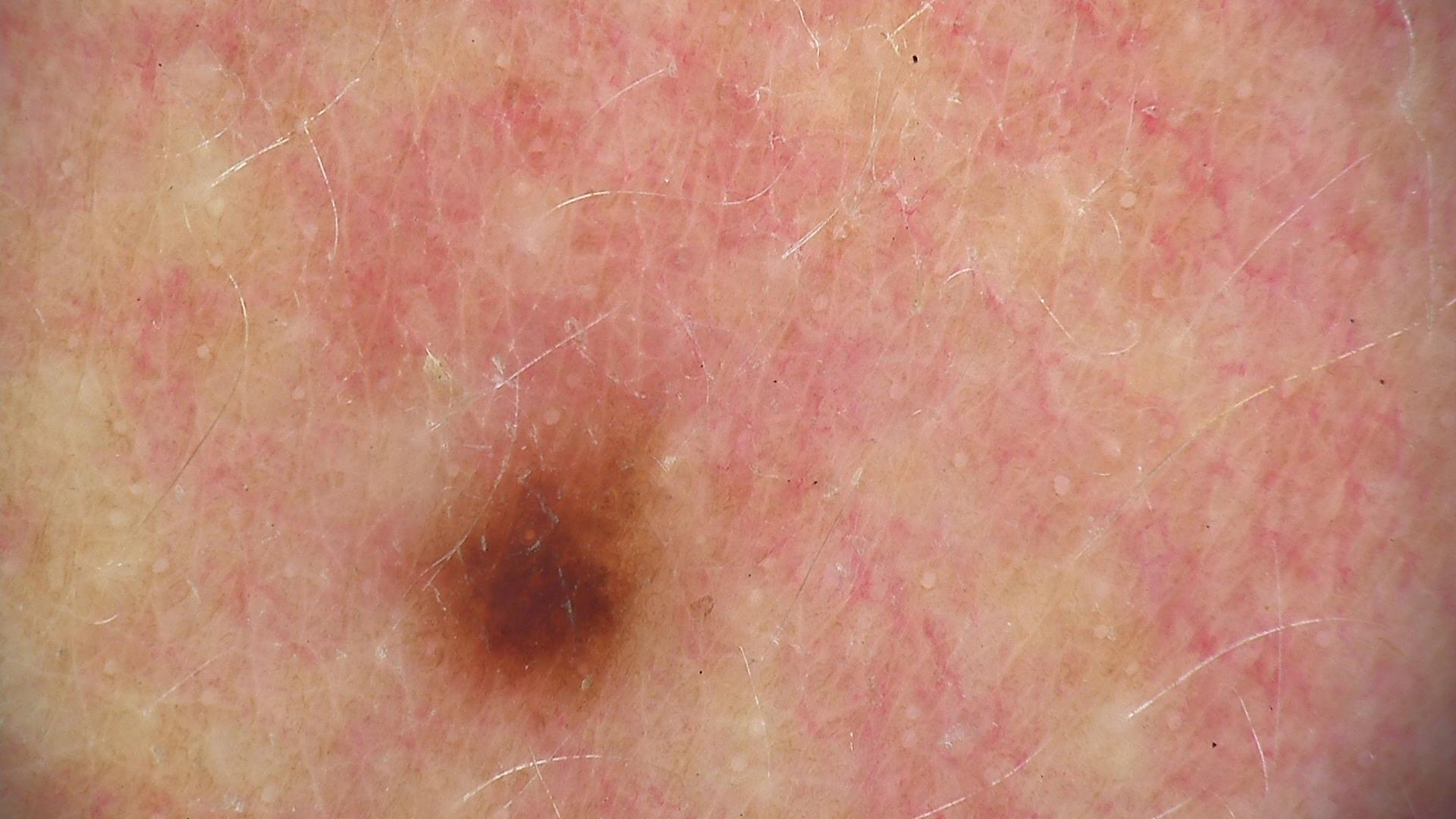Labeled as a benign lesion — a dysplastic junctional nevus.